The contributor is a female aged 18–29 · this is a close-up image · the contributor reports the lesion is flat · the patient reported no systemic symptoms · the patient considered this a rash · no relevant lesion symptoms reported — 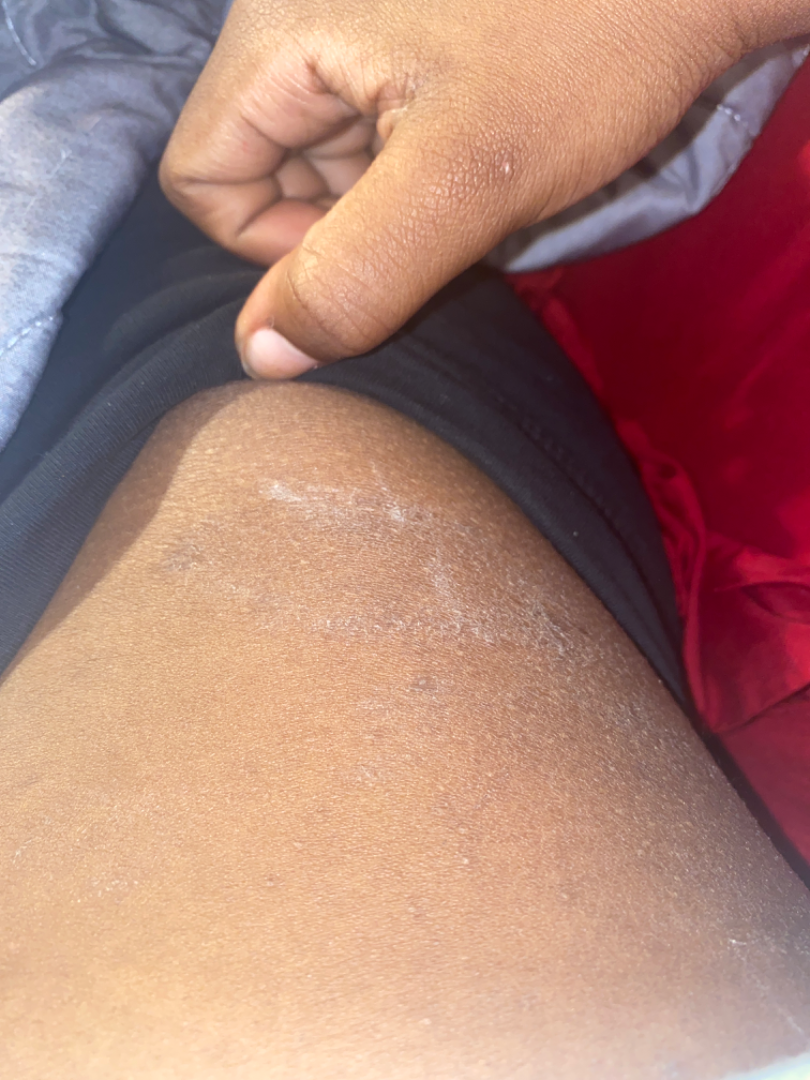assessment — the differential, in no particular order, includes Xerosis and Eczema.